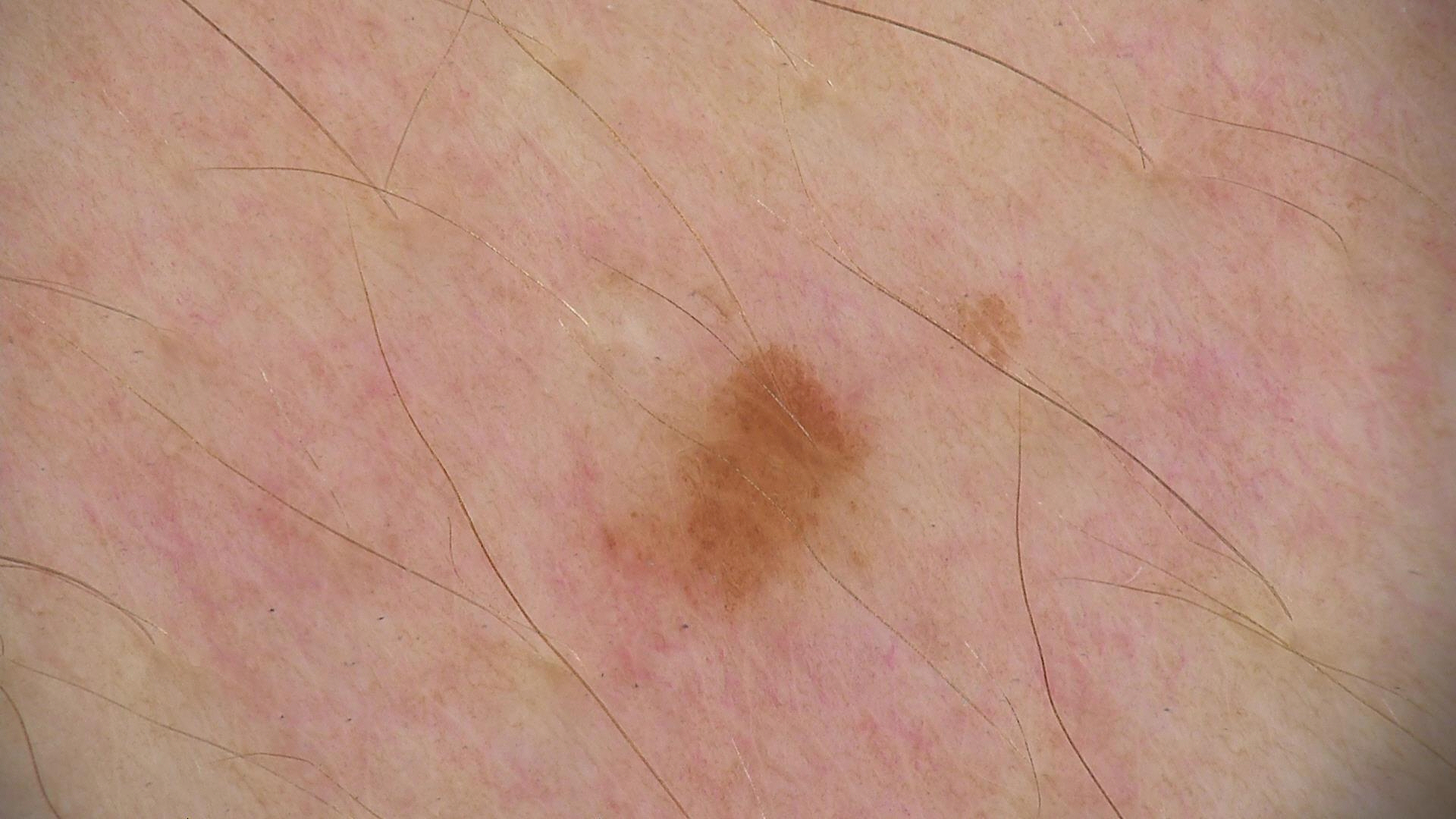Diagnosed as a dysplastic junctional nevus.